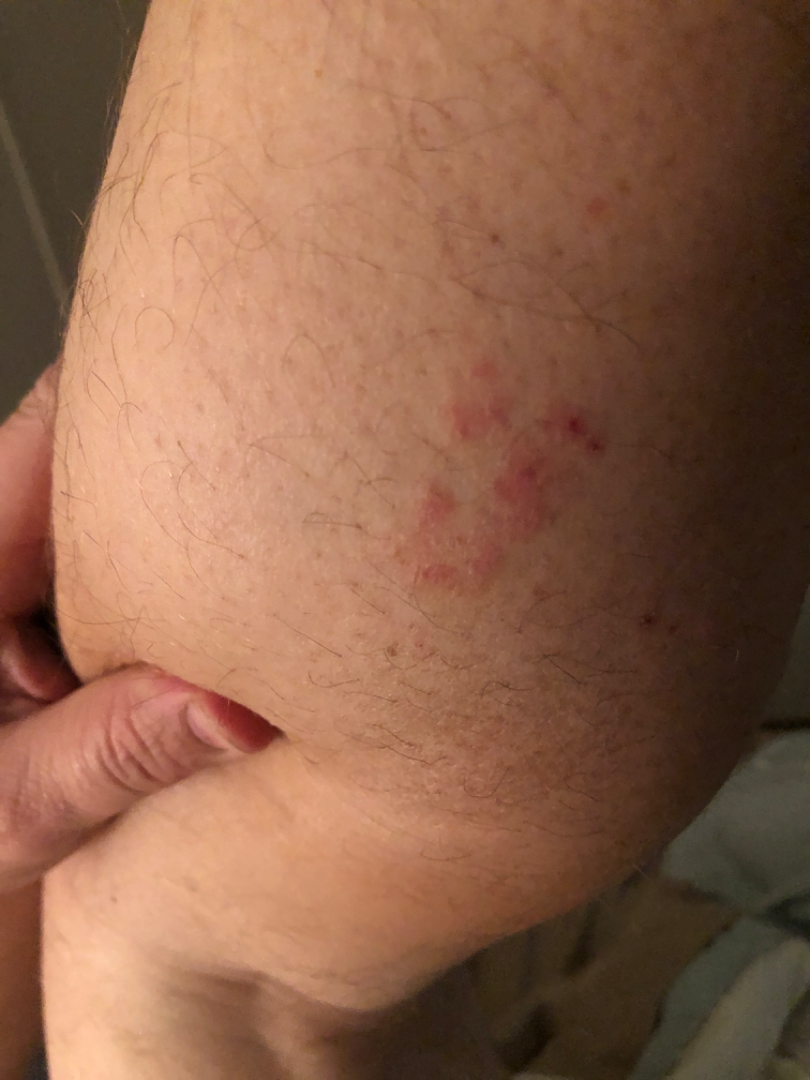assessment: indeterminate